A close-up photograph — 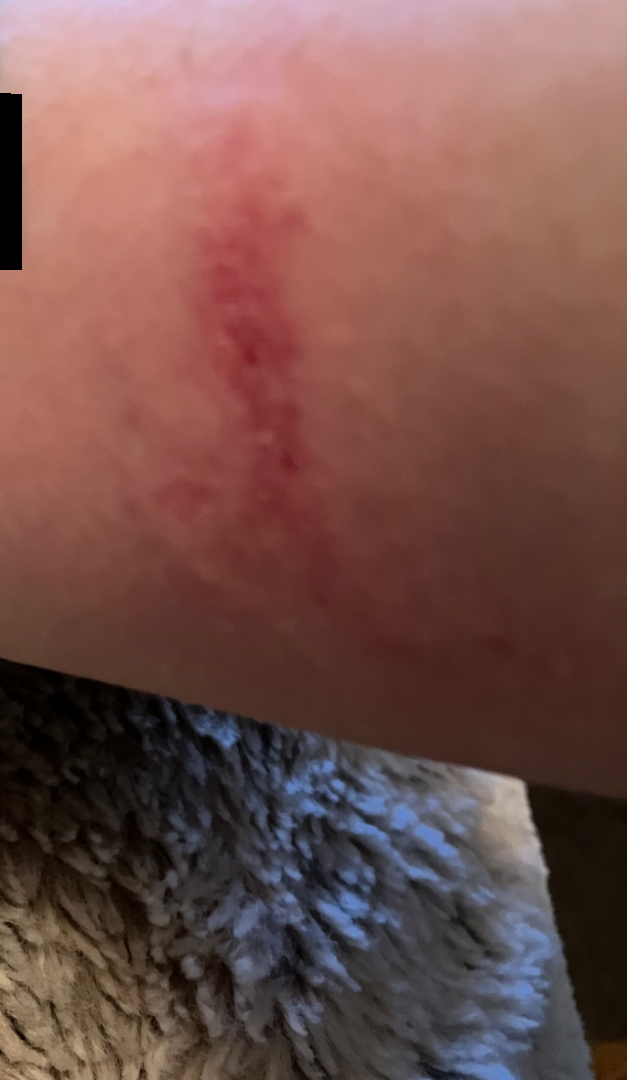<report>
  <assessment>ungradable on photographic review</assessment>
</report>